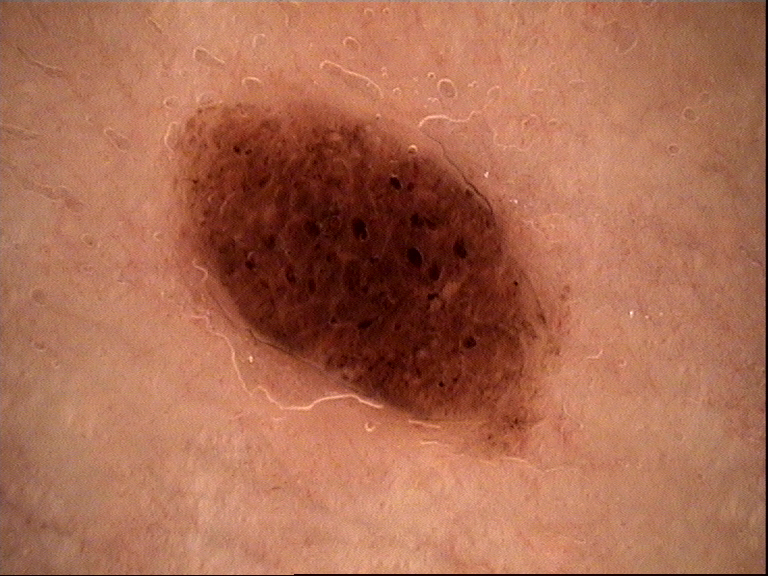Case:
Dermoscopy of a skin lesion.
Impression:
Consistent with a banal lesion — a compound nevus.